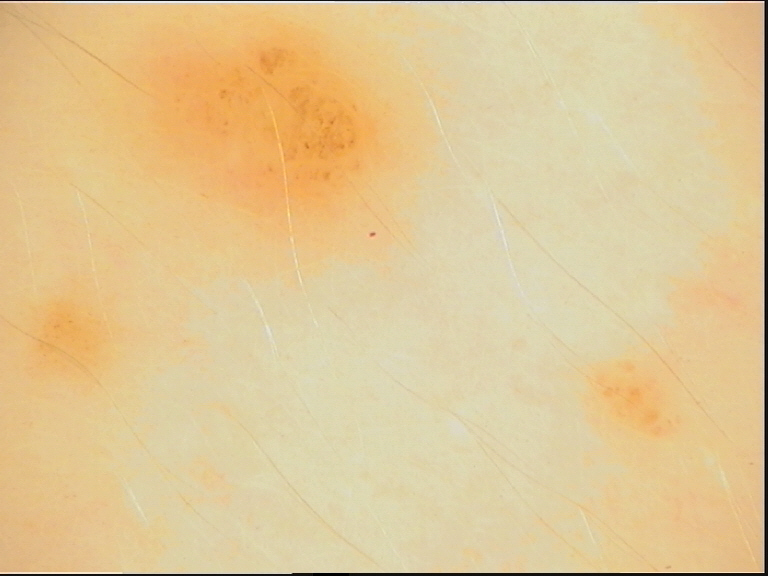The diagnosis was a dysplastic compound nevus.